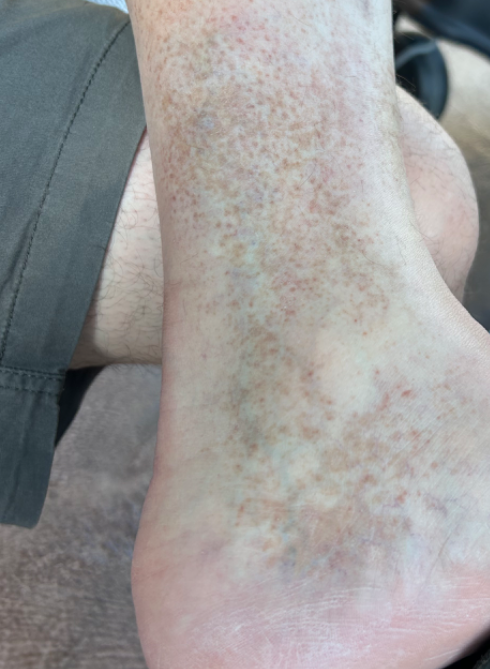described texture=flat | reported symptoms=bothersome appearance | location=leg | self-categorized as=skin that appeared healthy to them | onset=more than five years | framing=close-up | contributor=male, age 30–39 | diagnostic considerations=the primary impression is Pigmented purpuric eruption; an alternative is Stasis Dermatitis; also on the differential is Post-Inflammatory hyperpigmentation.